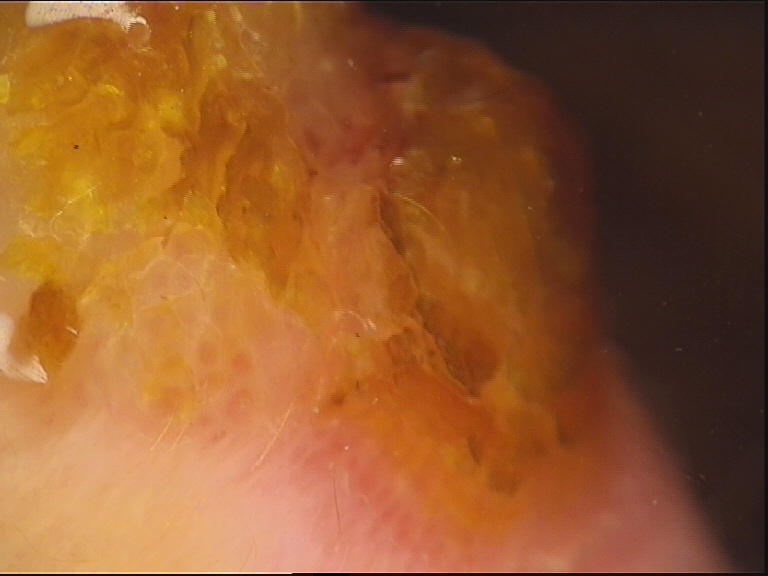A dermoscopic image of a skin lesion. Biopsy-confirmed as a squamous cell carcinoma.